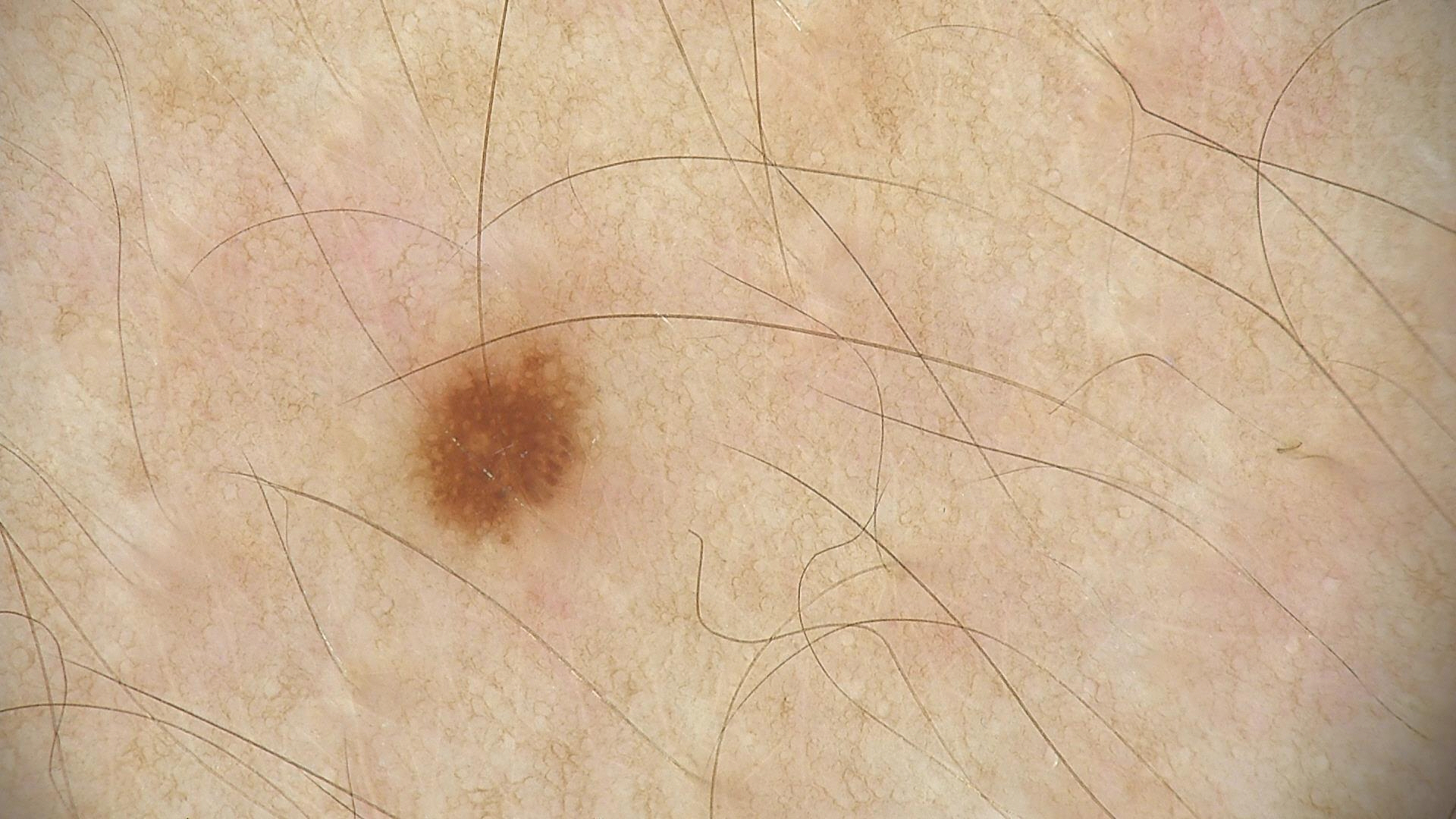imaging — dermoscopy; assessment — dysplastic junctional nevus (expert consensus).